A dermoscopic photograph of a skin lesion:
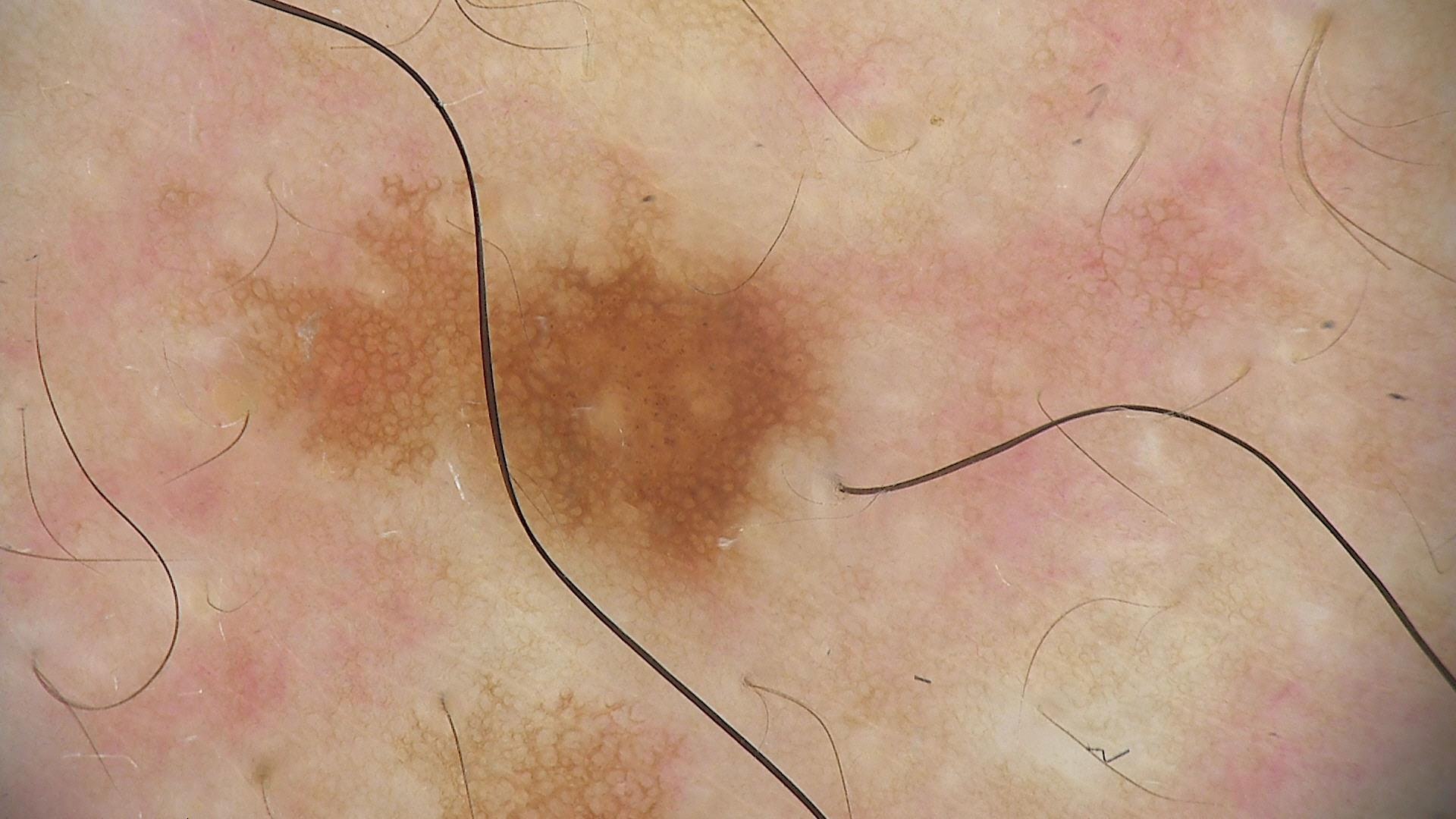Diagnosed as a dysplastic junctional nevus.